A skin lesion imaged with a dermatoscope.
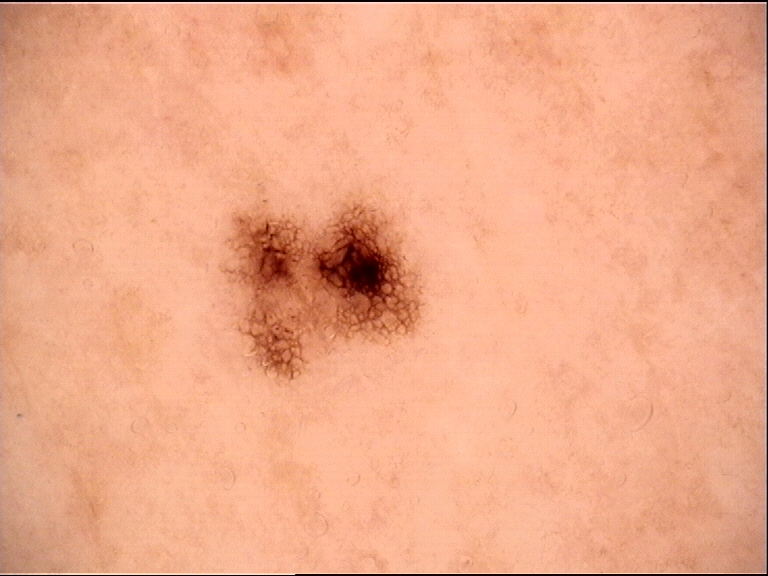diagnosis: dysplastic junctional nevus (expert consensus).